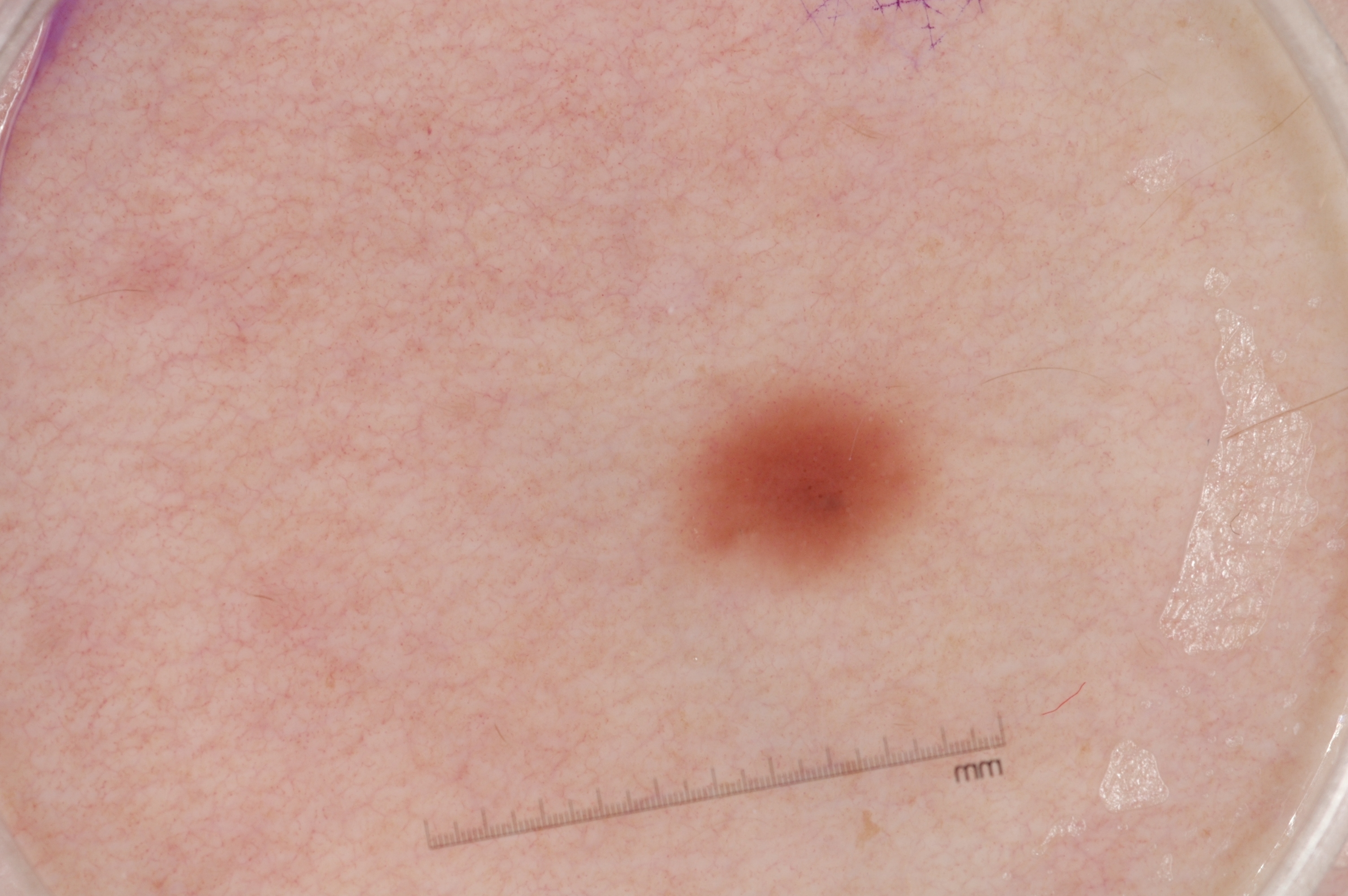A dermoscopic close-up of a skin lesion.
Dermoscopically, the lesion shows no pigment network, negative network, streaks, or milia-like cysts.
The visible lesion spans 674, 371, 937, 588.
A small lesion within a wider field of skin.
Histopathology confirmed a melanoma.